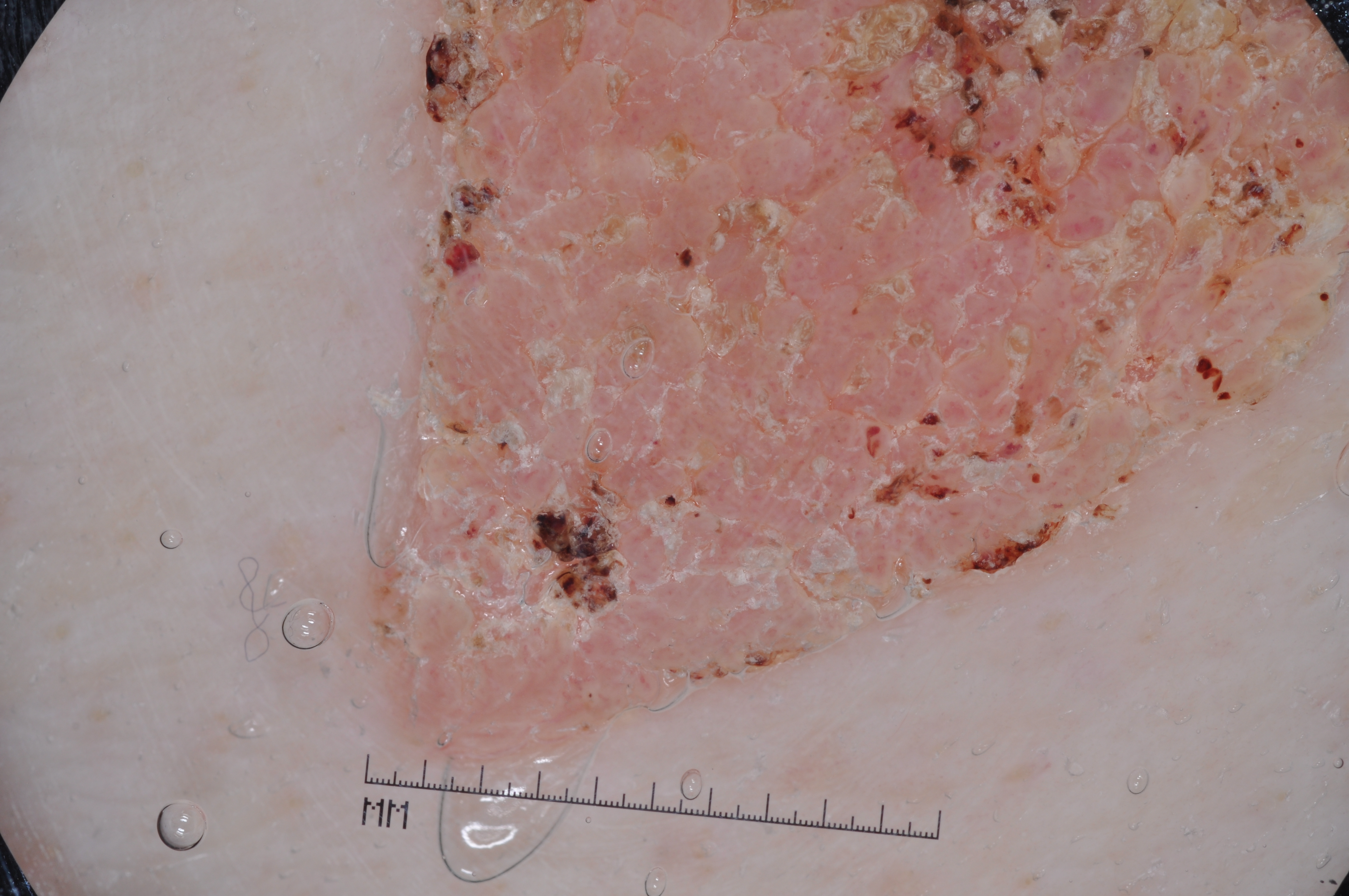A female patient, aged around 60. A dermatoscopic image of a skin lesion. The lesion is clipped by the edge of the image. Dermoscopic examination shows no milia-like cysts, negative network, streaks, or pigment network. With coordinates (x1, y1, x2, y2), the lesion's extent is bbox(295, 0, 1348, 784). Diagnosed as a seborrheic keratosis, a benign skin lesion.